Close-up view:
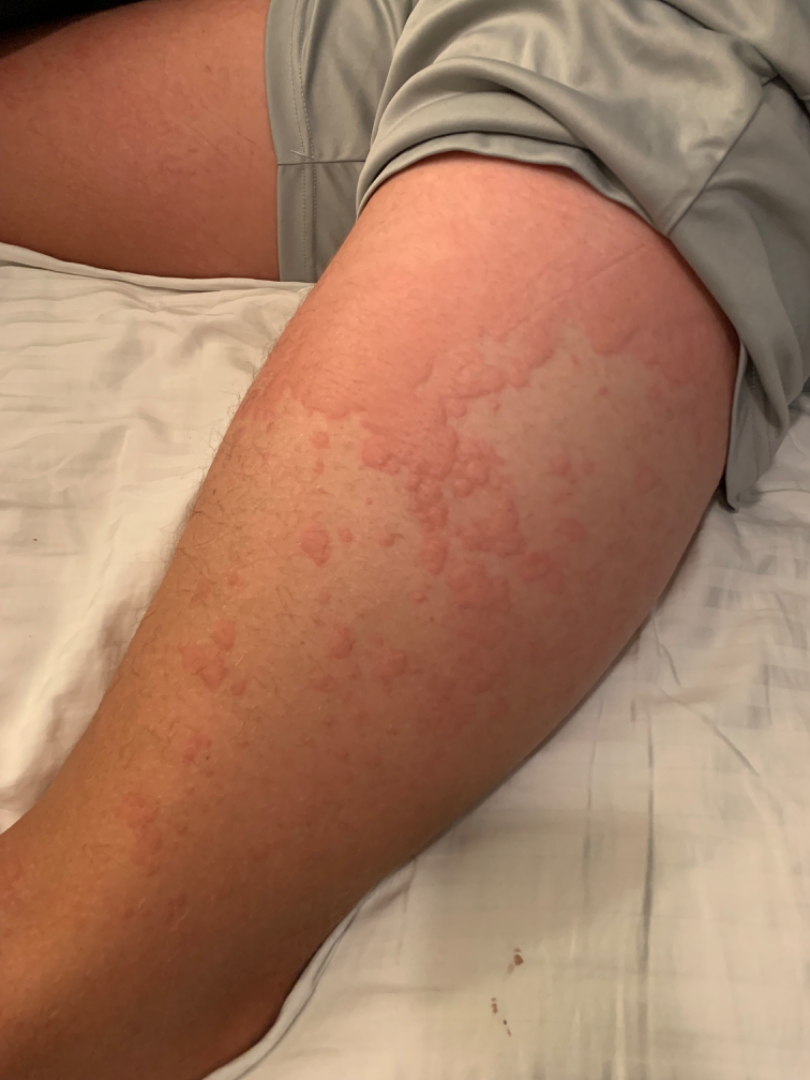| feature | finding |
|---|---|
| assessment | Urticaria (favored); Drug Rash (possible); Hypersensitivity (possible) |